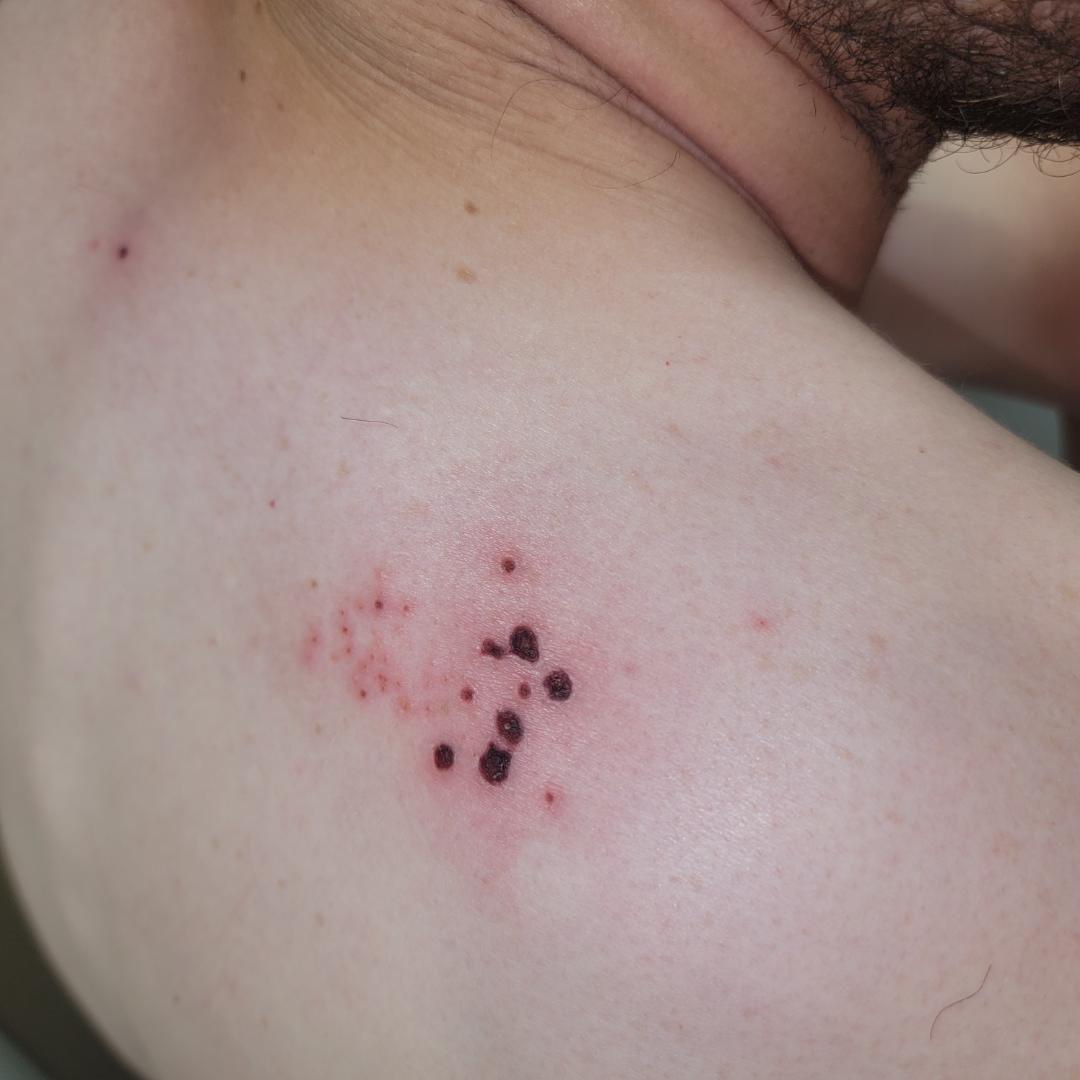The case was difficult to assess from the available photograph.